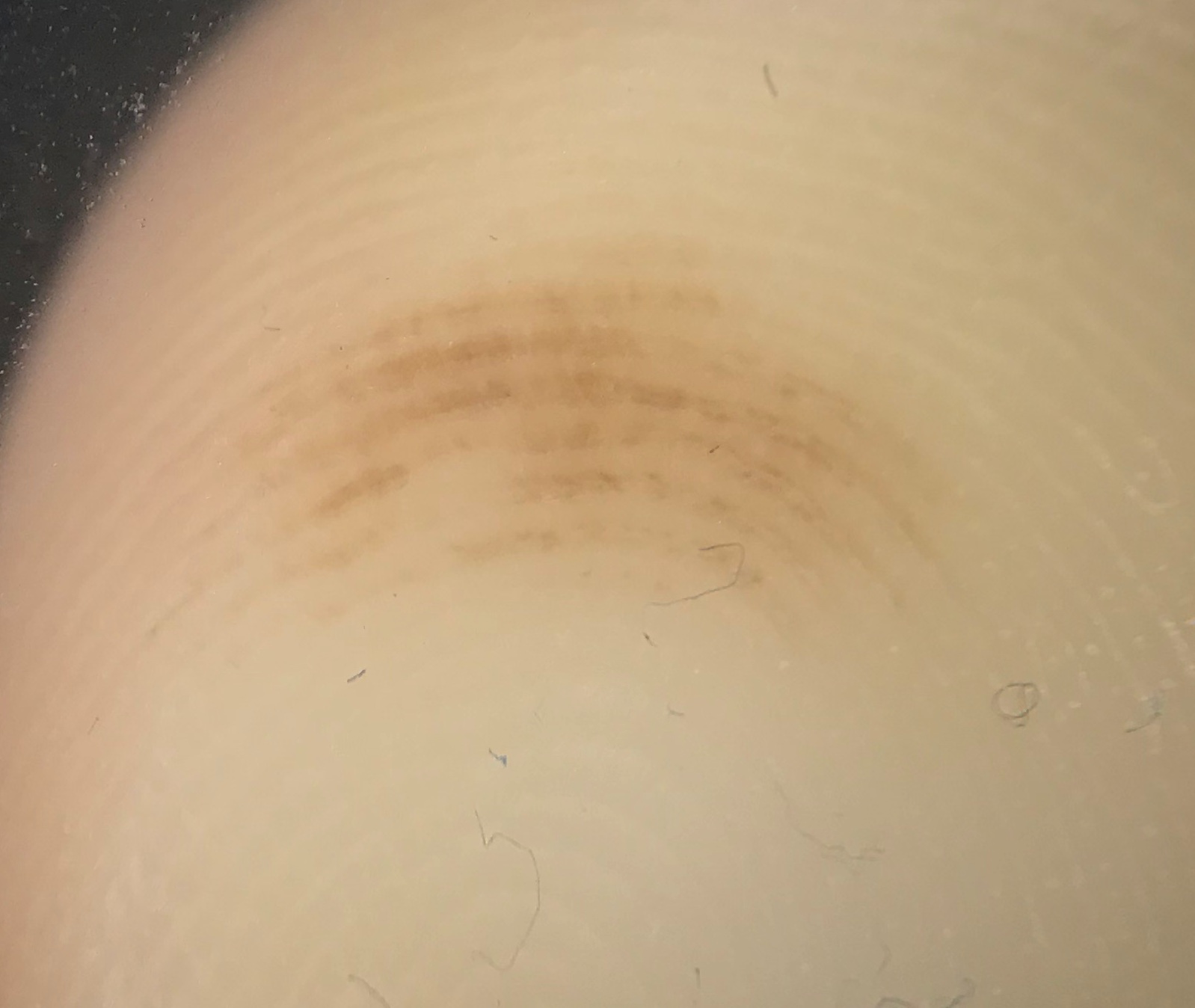Classified as an acral junctional nevus.